A dermoscopic photograph of a skin lesion; a female subject approximately 70 years of age.
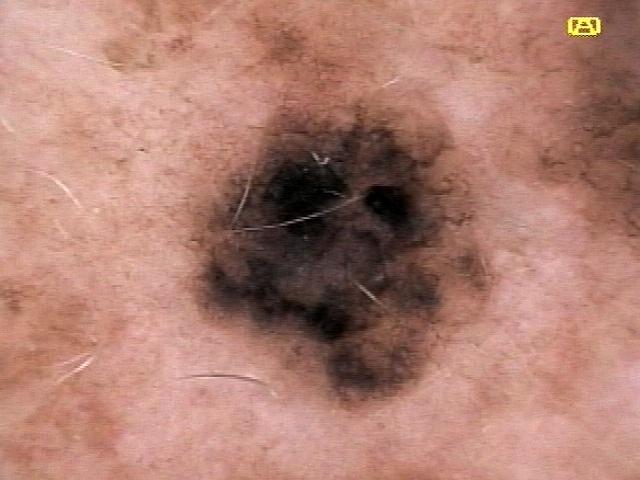{"lesion_location": {"region": "the trunk", "detail": "the posterior trunk"}, "diagnosis": {"name": "Nevus", "malignancy": "benign", "confirmation": "histopathology", "lineage": "melanocytic"}}